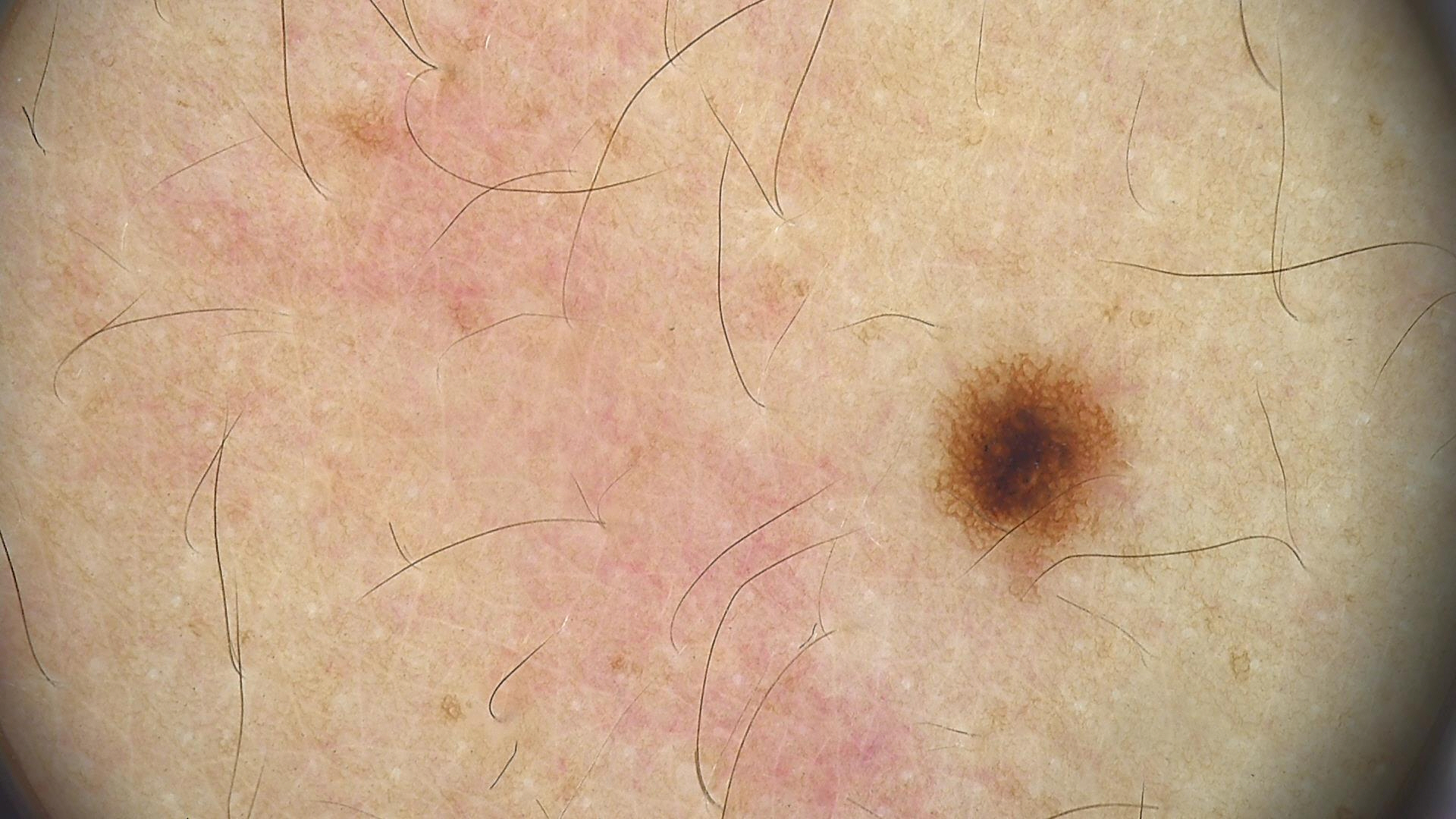Summary: Dermoscopy of a skin lesion. Conclusion: Diagnosed as a benign lesion — a dysplastic junctional nevus.